A skin lesion imaged with a dermatoscope:
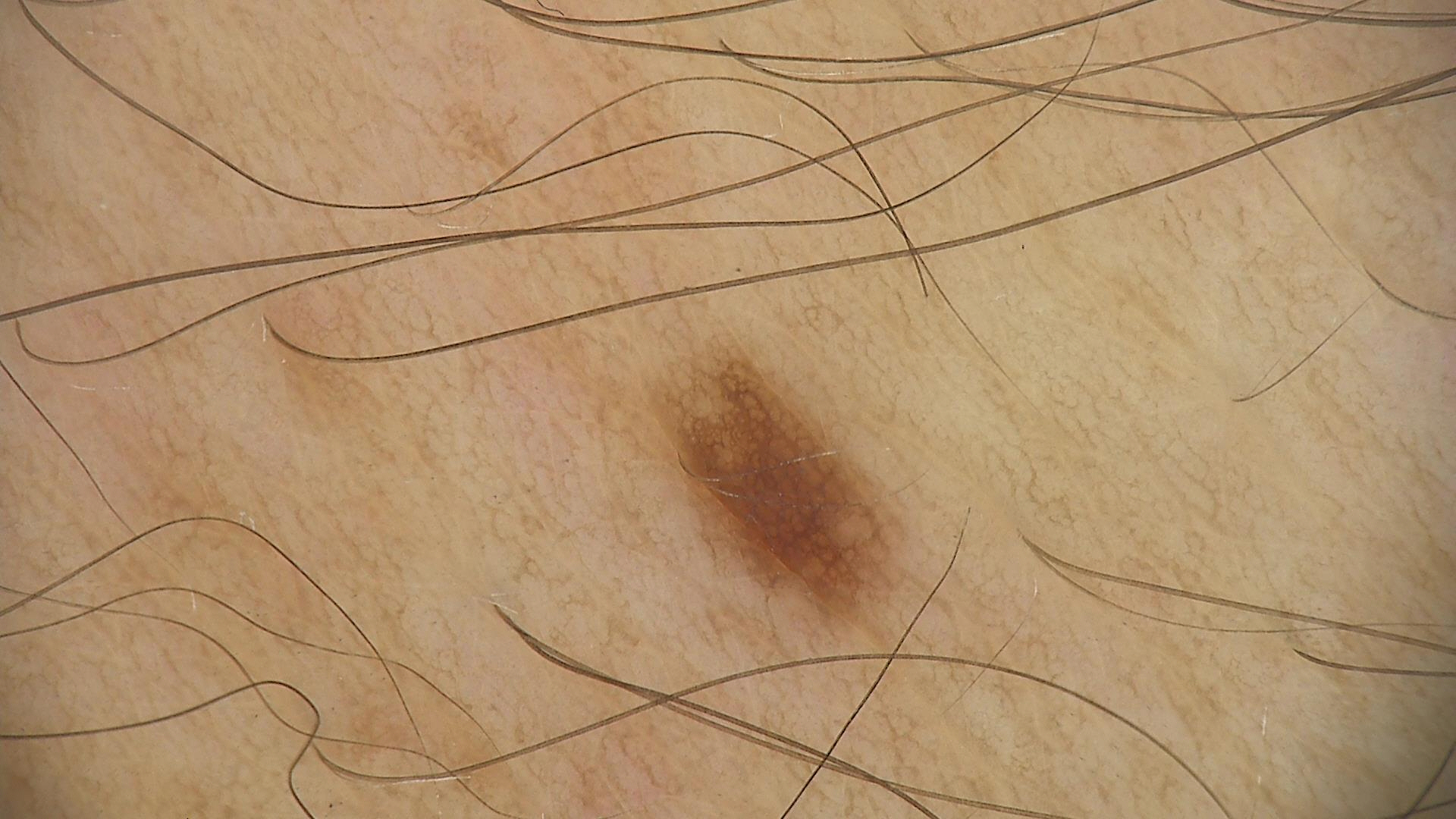– assessment · dysplastic junctional nevus (expert consensus)